The arm is involved · this is a close-up image:
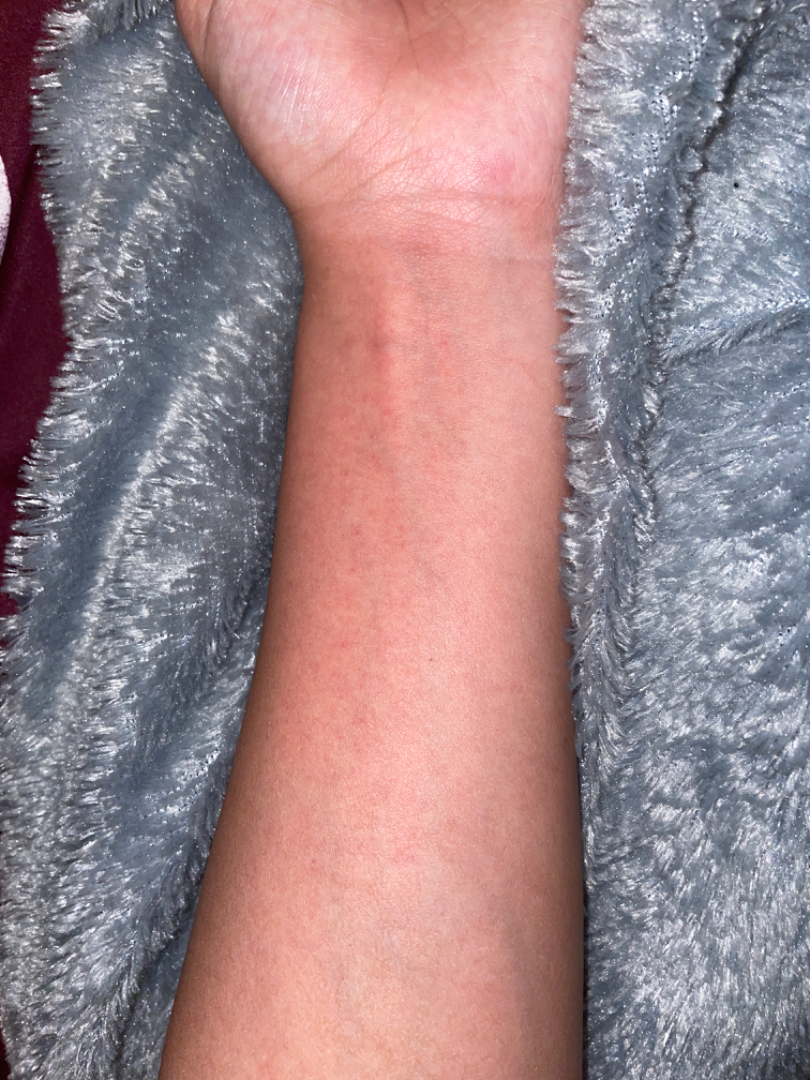Findings:
The condition could not be reliably identified from the image.